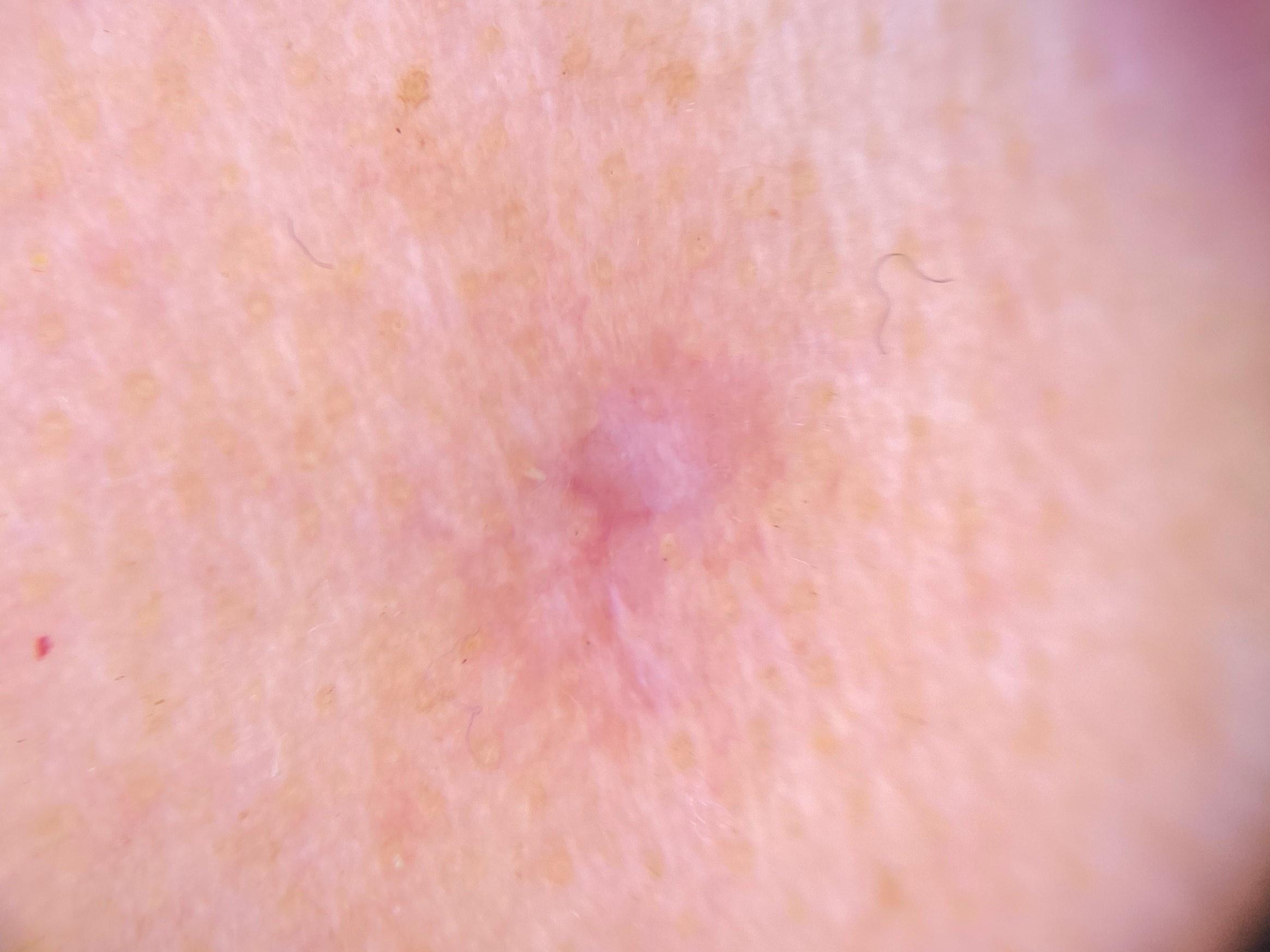A female subject aged 83 or over. Recorded as Fitzpatrick phototype II. A dermoscopic close-up of a skin lesion. The lesion involves the head or neck. Histopathological examination showed a malignant, epidermal lesion — a squamous cell carcinoma.